A close-up photograph; the patient is 50–59, female; the sole of the foot, back of the torso, leg, head or neck, front of the torso and top or side of the foot are involved:
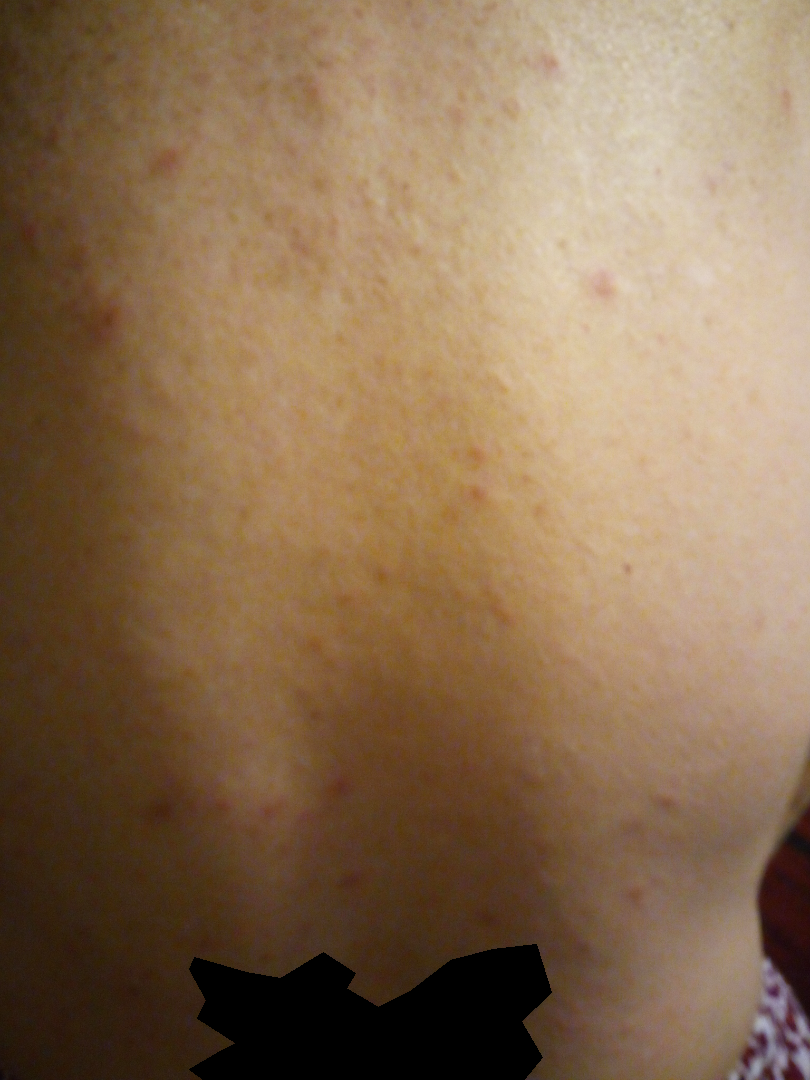Texture is reported as rough or flaky, fluid-filled and raised or bumpy. Self-categorized by the patient as a rash. Reported duration is one to four weeks. Associated systemic symptoms include fatigue and joint pain. The lesion is associated with burning, itching, enlargement, bleeding and bothersome appearance. Folliculitis (most likely).